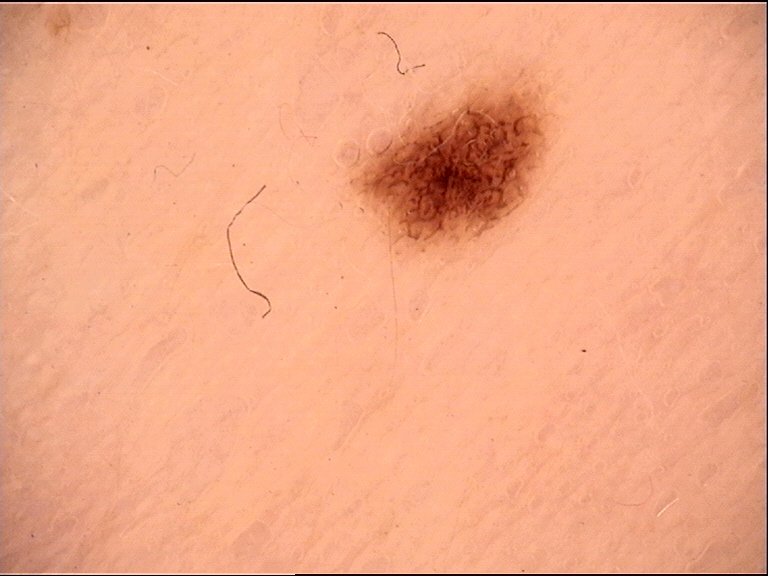Summary:
A dermoscopic image of a skin lesion.
Impression:
Diagnosed as a benign lesion — a dysplastic junctional nevus.